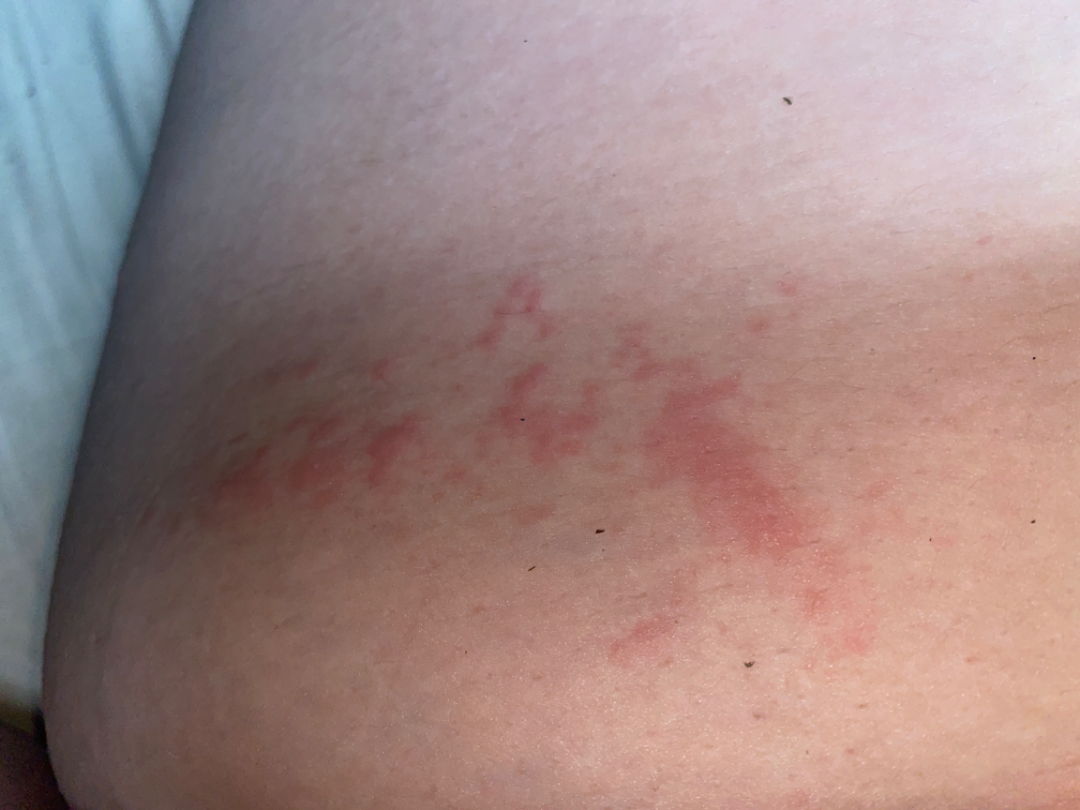The photograph is a close-up of the affected area. The patient is a female aged 18–29. Symptoms reported: itching. Self-categorized by the patient as a rash. The patient reports the lesion is flat. The patient reports the condition has been present for less than one week. Favoring Urticaria; with consideration of Allergic Contact Dermatitis; possibly Herpes Zoster; less probable is Acute dermatitis, NOS; less likely is Insect Bite.